The photograph is a close-up of the affected area; the head or neck is involved; male subject, age 30–39 — 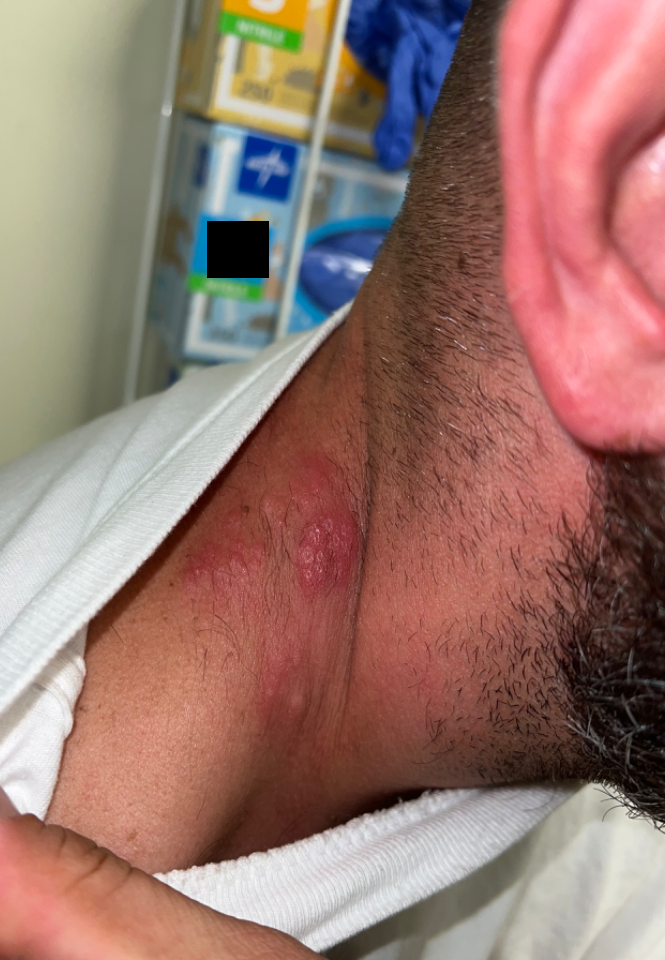{
  "texture": "raised or bumpy",
  "duration": "less than one week",
  "differential": {
    "leading": [
      "Herpes Simplex"
    ]
  }
}